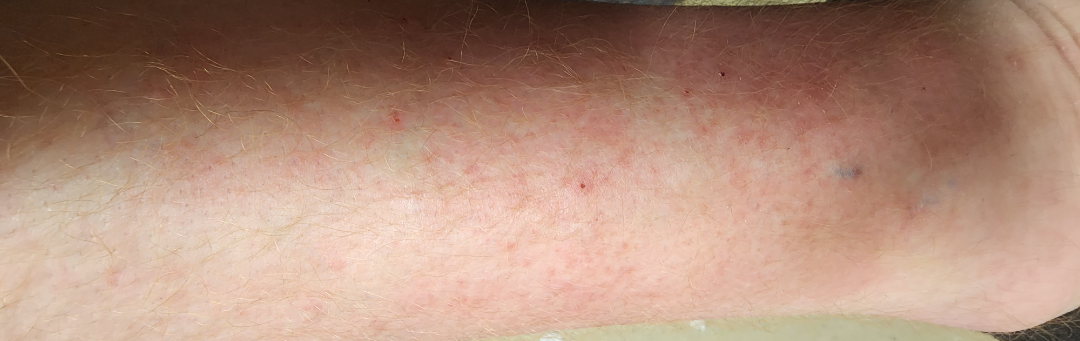patient: male, age 30–39
texture: raised or bumpy
symptoms:
  - enlargement
  - bleeding
  - burning
  - bothersome appearance
  - itching
systemic_symptoms: none reported
shot_type: close-up
body_site:
  - leg
  - arm
  - front of the torso
  - back of the hand
differential:
  tied_lead:
    - Contact dermatitis
    - Stasis Dermatitis